Female subject, age 60–69. The photograph is a close-up of the affected area. The back of the torso, arm and leg are involved.
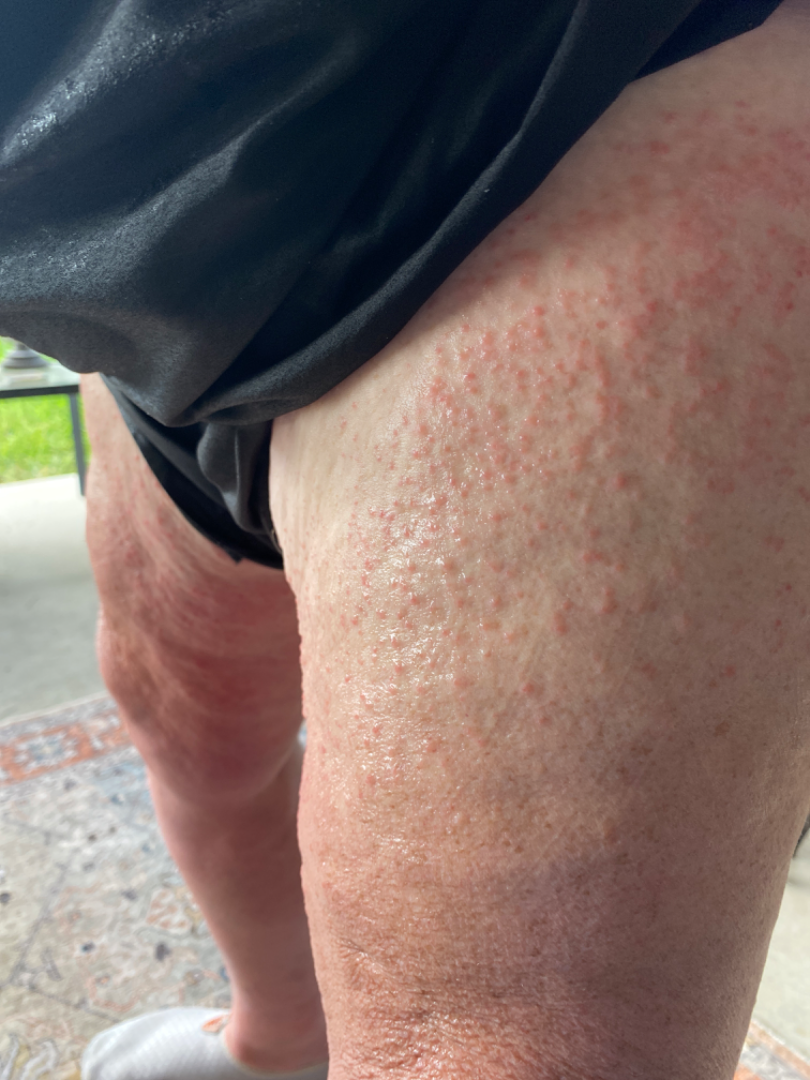The differential, in no particular order, includes Photodermatitis and Allergic Contact Dermatitis.